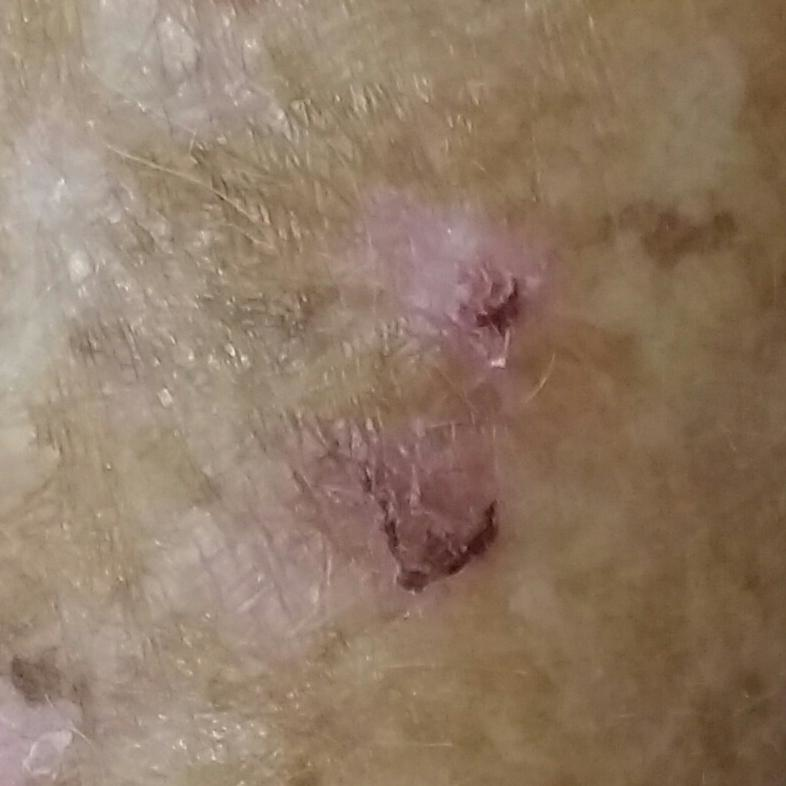skin type: II; patient: female, aged 82; image: smartphone clinical photo; body site: a forearm; lesion diameter: 9 × 7 mm; diagnosis: actinic keratosis (clinical consensus).